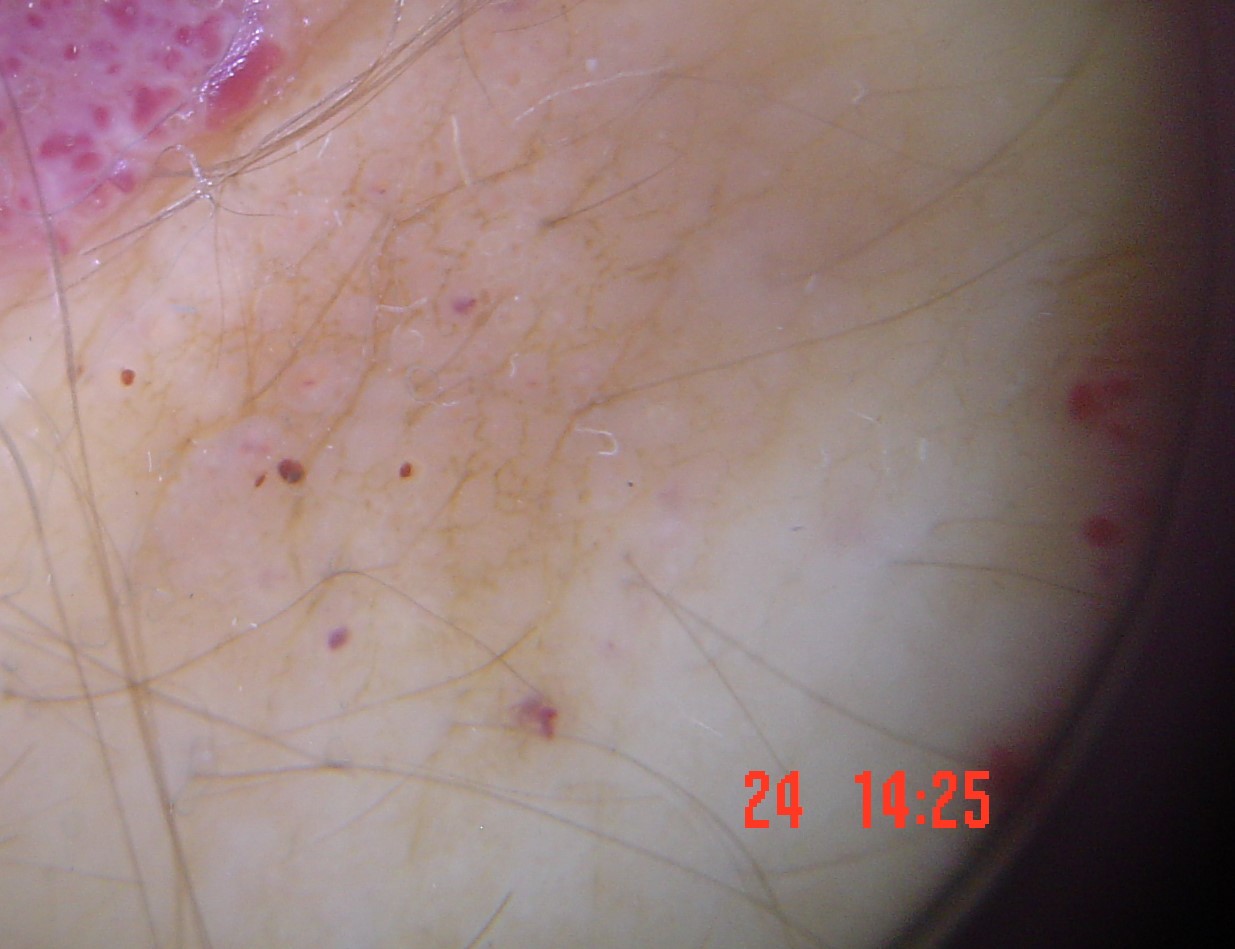A skin lesion imaged with a dermatoscope.
Labeled as a lymphangioma.